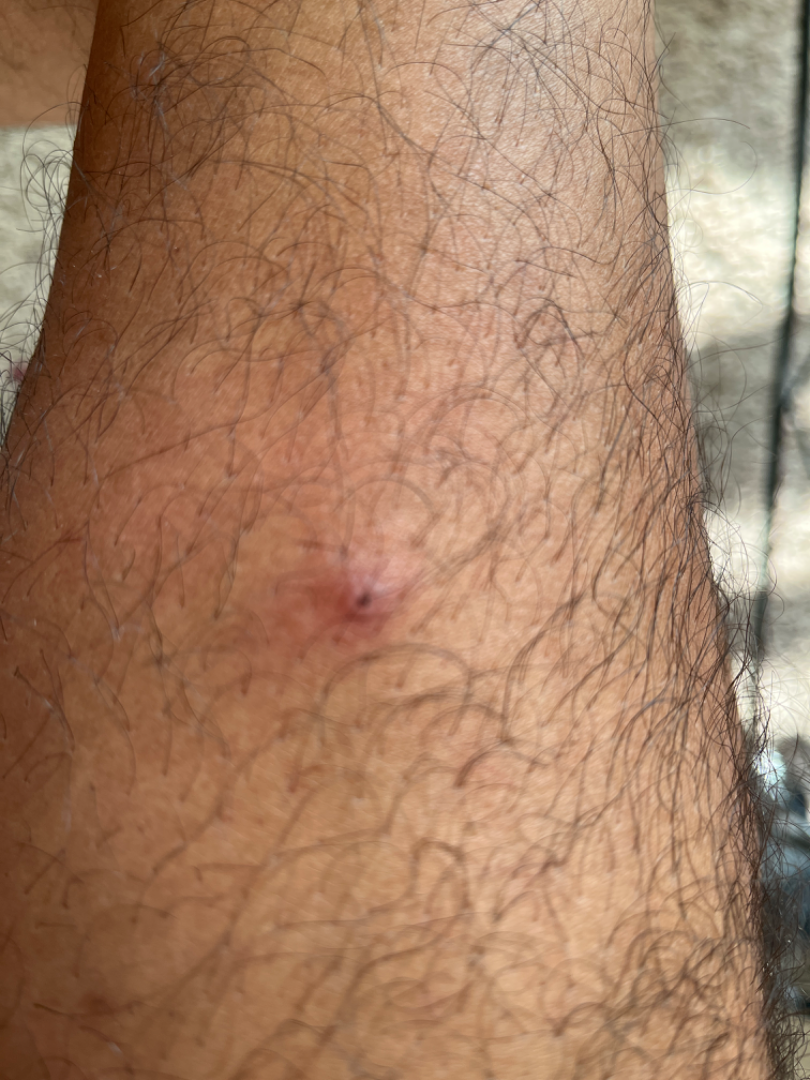A close-up photograph. The leg is involved. Fitzpatrick phototype V; lay reviewers estimated 5 on the Monk skin tone scale. The subject is male. The patient described the issue as a rash. The patient notes itching. Texture is reported as raised or bumpy. On teledermatology review: most consistent with Abscess.